A skin lesion imaged with a dermatoscope.
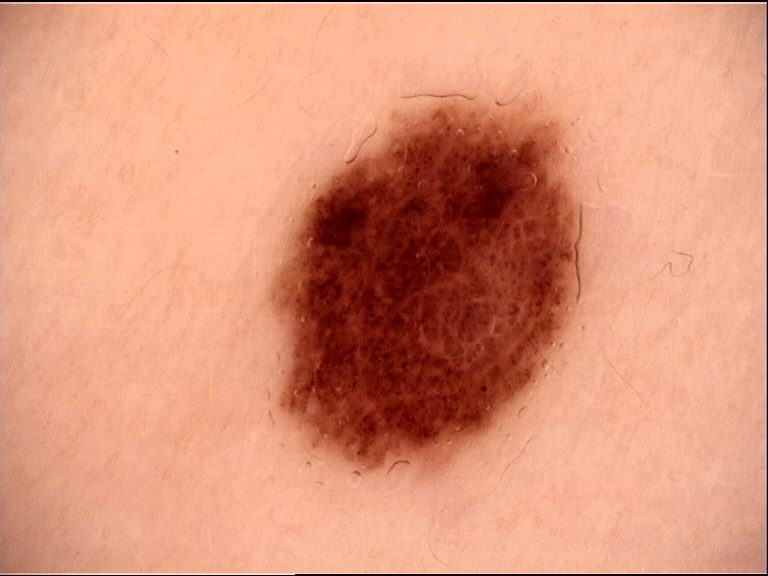Labeled as a benign lesion — a dysplastic compound nevus.